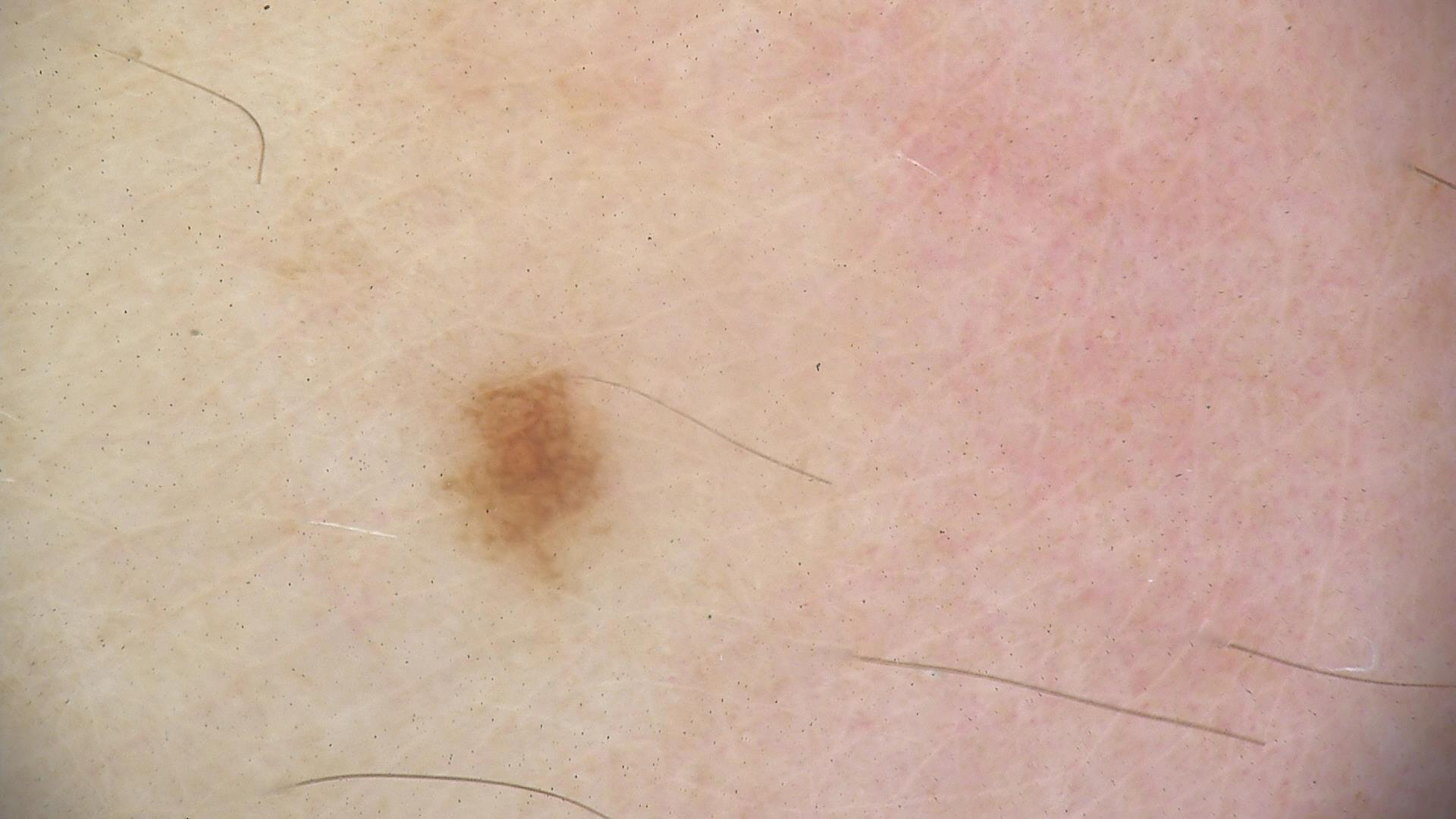  diagnosis:
    name: dysplastic junctional nevus
    code: jd
    malignancy: benign
    super_class: melanocytic
    confirmation: expert consensus